Skin tone: Fitzpatrick VI · the photograph is a close-up of the affected area:
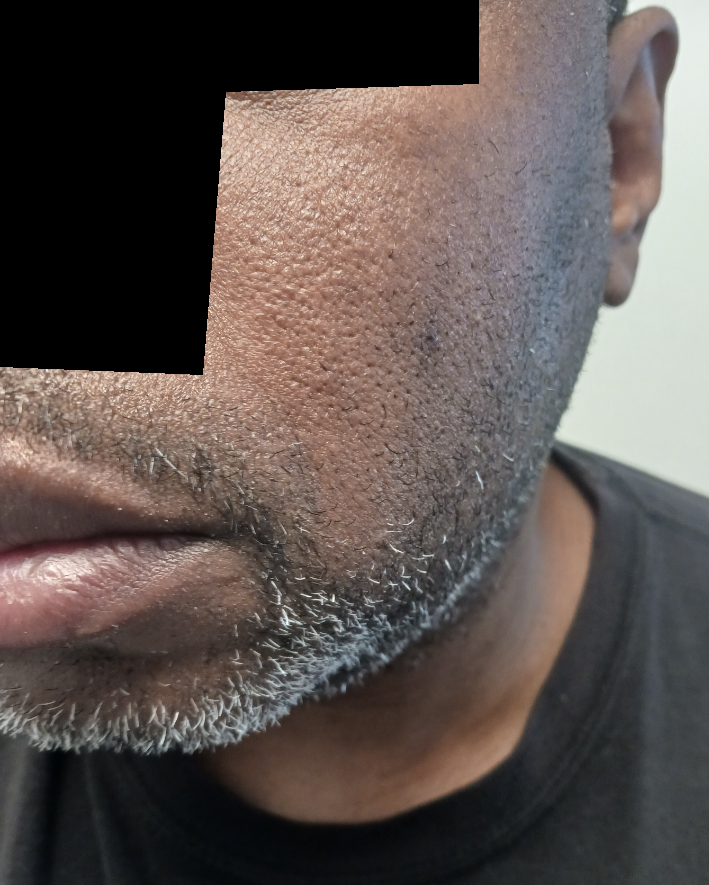assessment: no discernible pathology